Located on the leg and top or side of the foot; a close-up photograph.
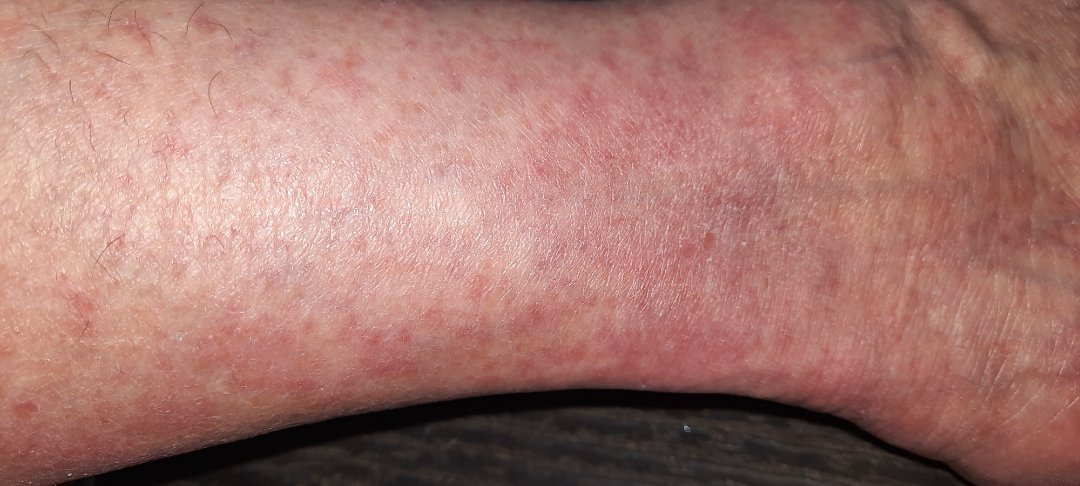{
  "assessment": "unable to determine"
}